A dermatoscopic image of a skin lesion, a male subject roughly 30 years of age — 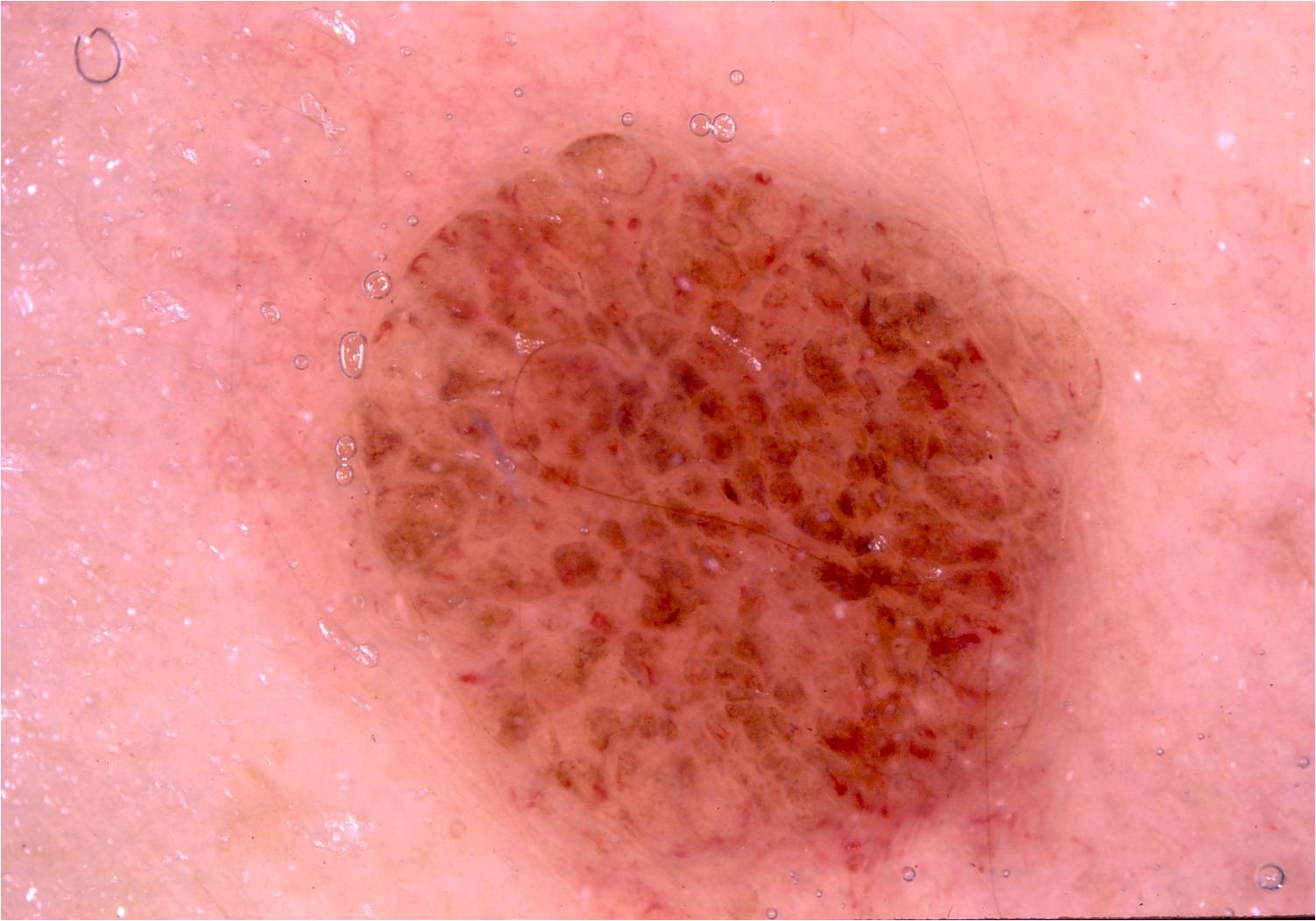Q: What is the lesion's bounding box?
A: x1=315, y1=126, x2=1112, y2=918
Q: Which assessed dermoscopic features were absent?
A: negative network, globules, streaks, milia-like cysts, and pigment network
Q: Lesion extent?
A: large
Q: What did the assessment conclude?
A: a melanocytic nevus, a benign lesion